A dermoscopic photograph of a skin lesion.
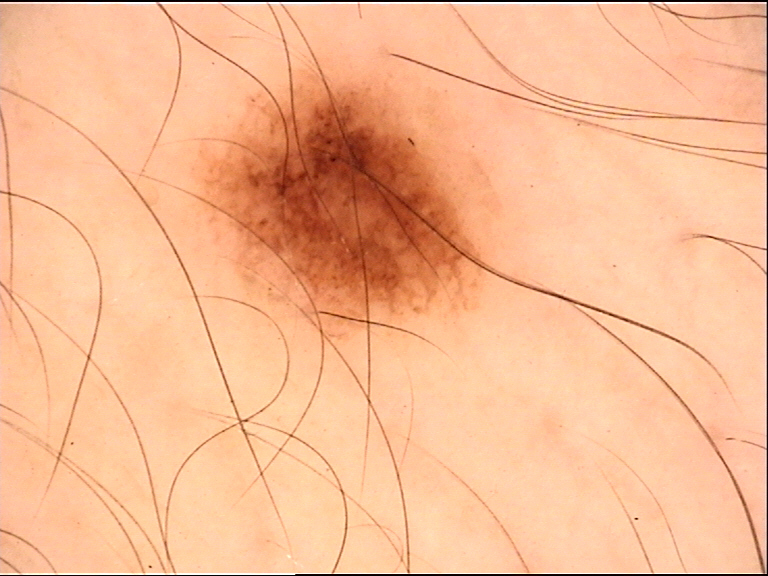Findings:
This is a banal lesion.
Impression:
Labeled as a junctional nevus.